A dermatoscopic image of a skin lesion.
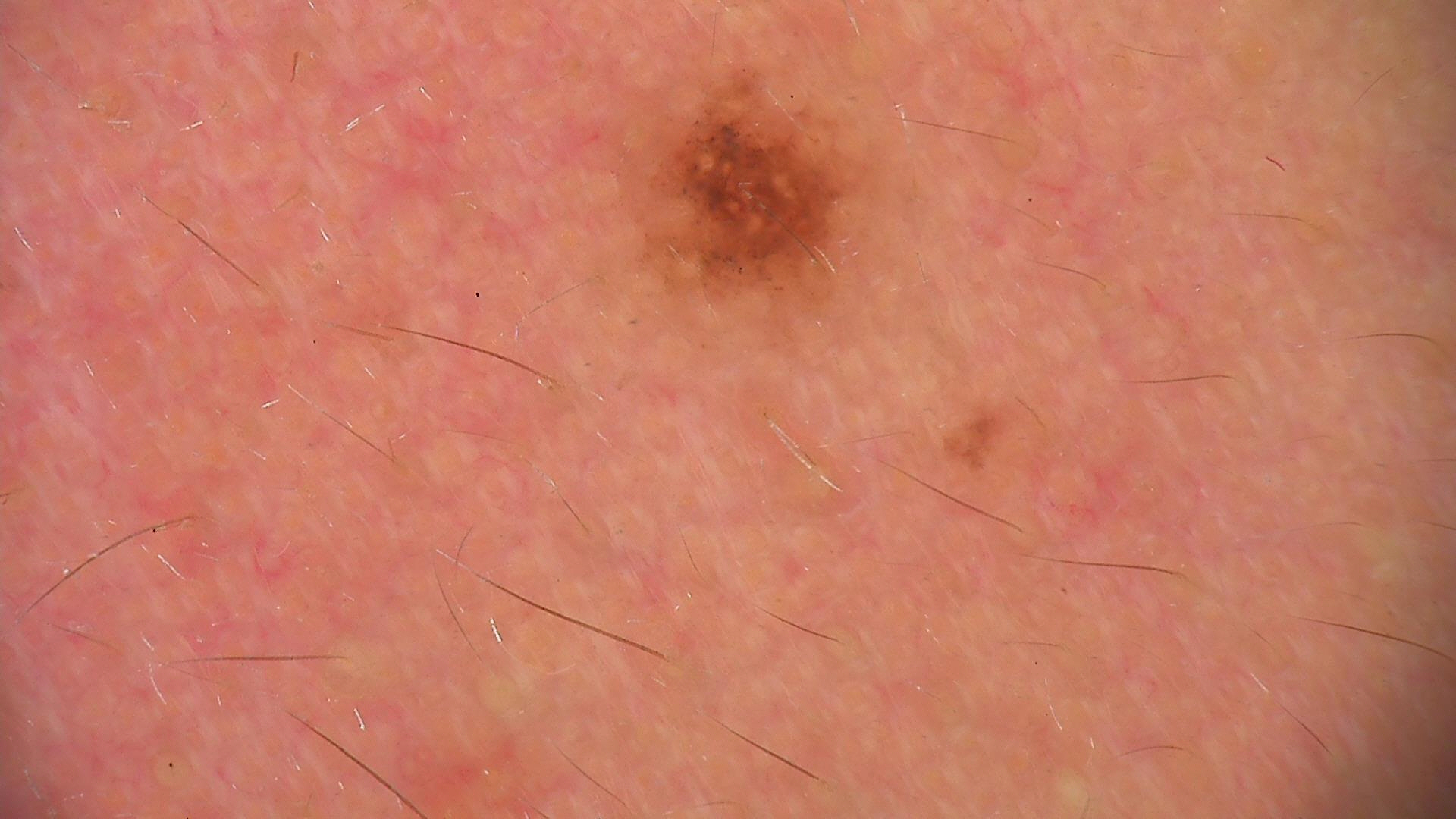Classified as a compound lesion — a Miescher nevus.